The photo was captured at a distance · located on the front of the torso.
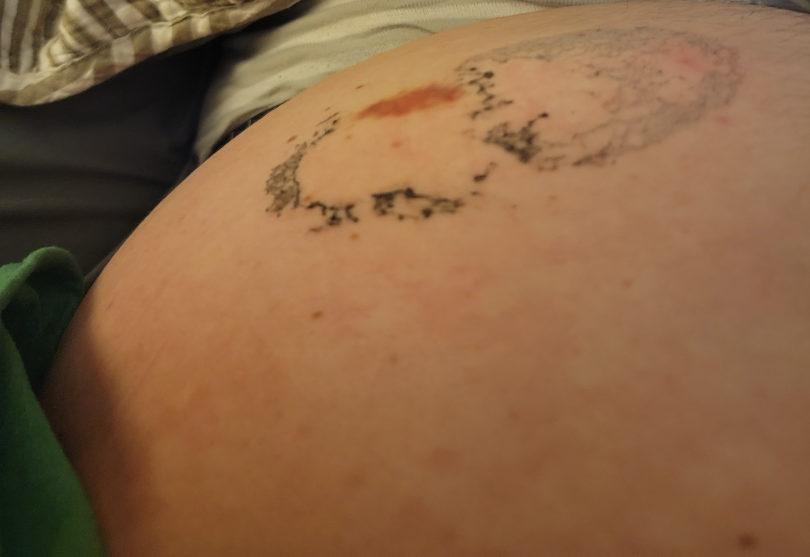Findings: Diagnostic features were not clearly distinguishable in this photograph.